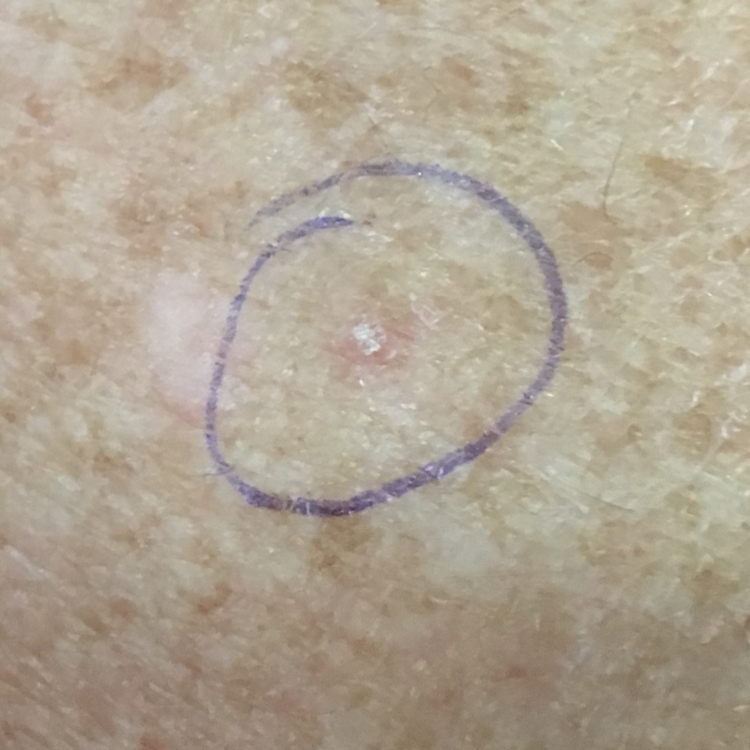Q: Tell me about the patient.
A: in their late 60s
Q: What is the imaging modality?
A: smartphone clinical photo
Q: What is the anatomic site?
A: a forearm
Q: What does the patient describe?
A: itching / no pain
Q: What is this lesion?
A: actinic keratosis (clinical consensus)